A skin lesion imaged with a dermatoscope, a female patient approximately 70 years of age: 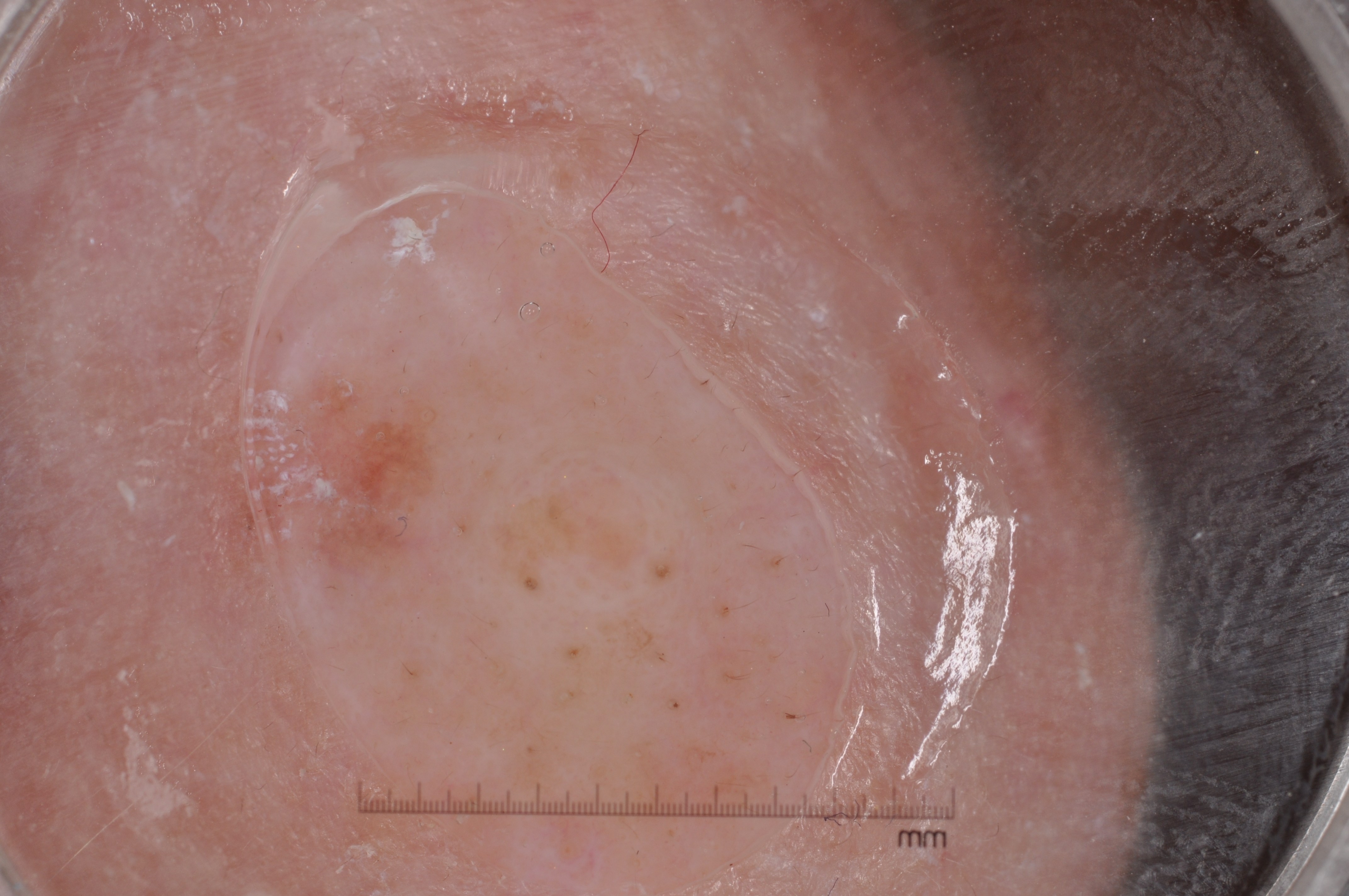Q: Where is the lesion located?
A: x1=494 y1=443 x2=706 y2=615
Q: How much of the field does the lesion occupy?
A: ~2% of the field
Q: Which dermoscopic features are absent?
A: negative network, streaks, milia-like cysts, and pigment network
Q: What did the assessment conclude?
A: a melanocytic nevus, a benign skin lesion